The chart notes a first-degree relative with melanoma but no previous melanoma; Fitzpatrick phototype III; contact-polarized dermoscopy of a skin lesion — 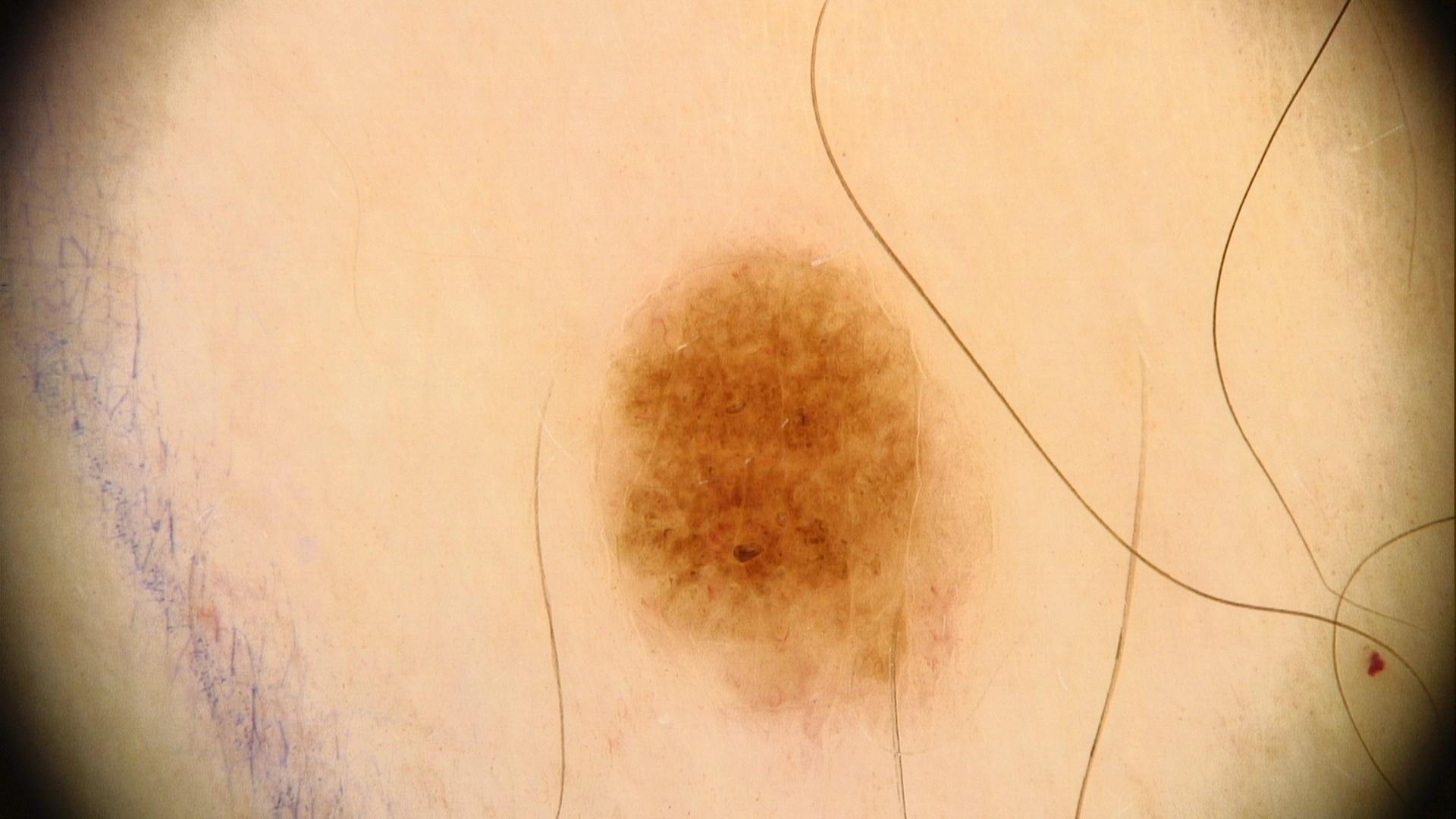Q: What is this lesion?
A: Nevus (clinical impression)